A dermoscopy image of a single skin lesion.
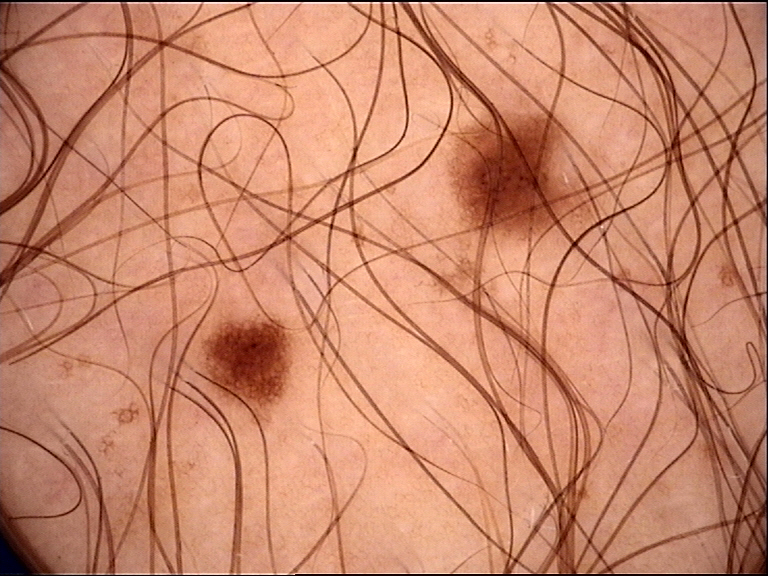Classified as a dysplastic junctional nevus.